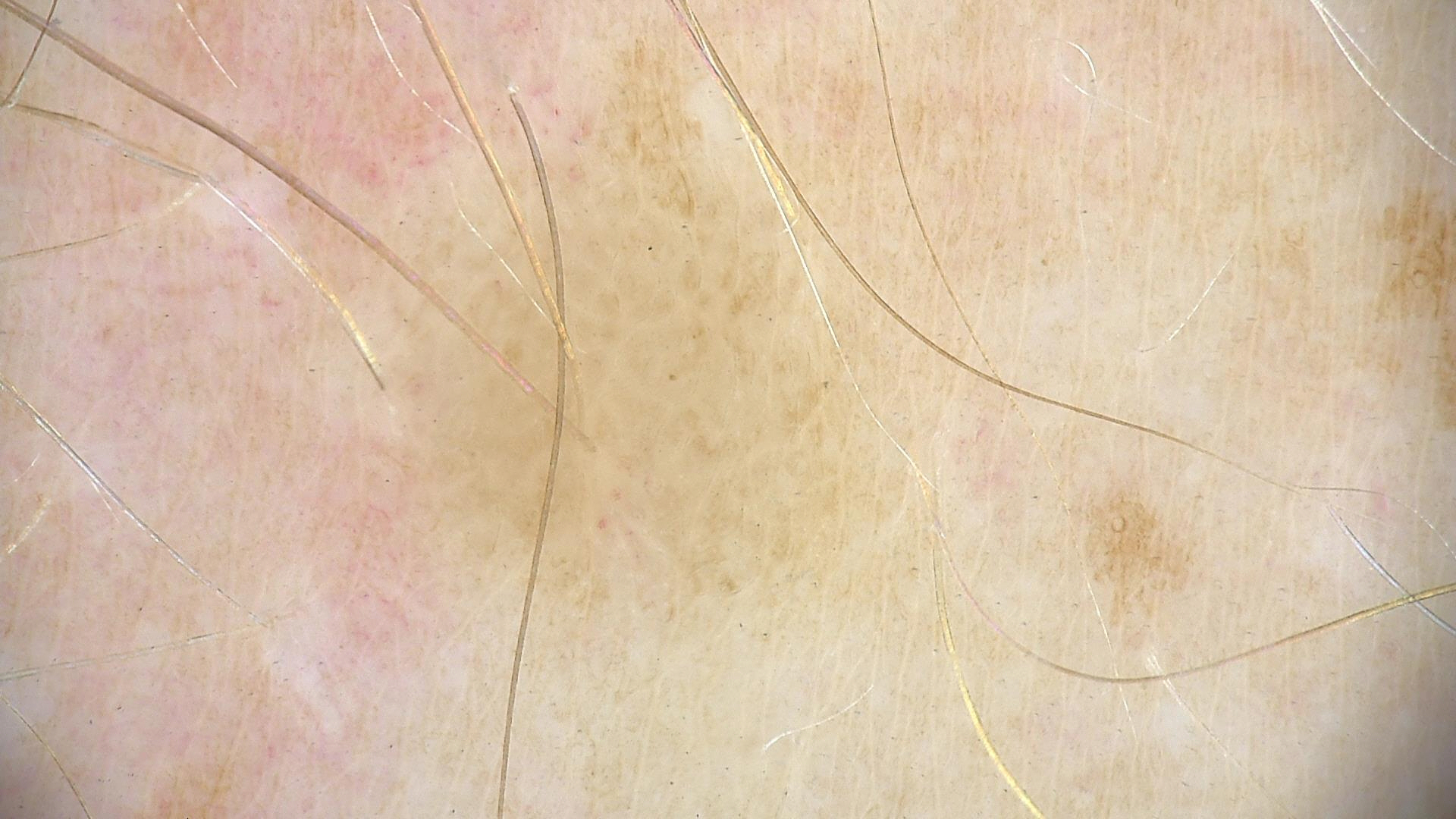Diagnosed as a seborrheic keratosis.